A female patient aged around 70; a skin lesion imaged with a dermatoscope: 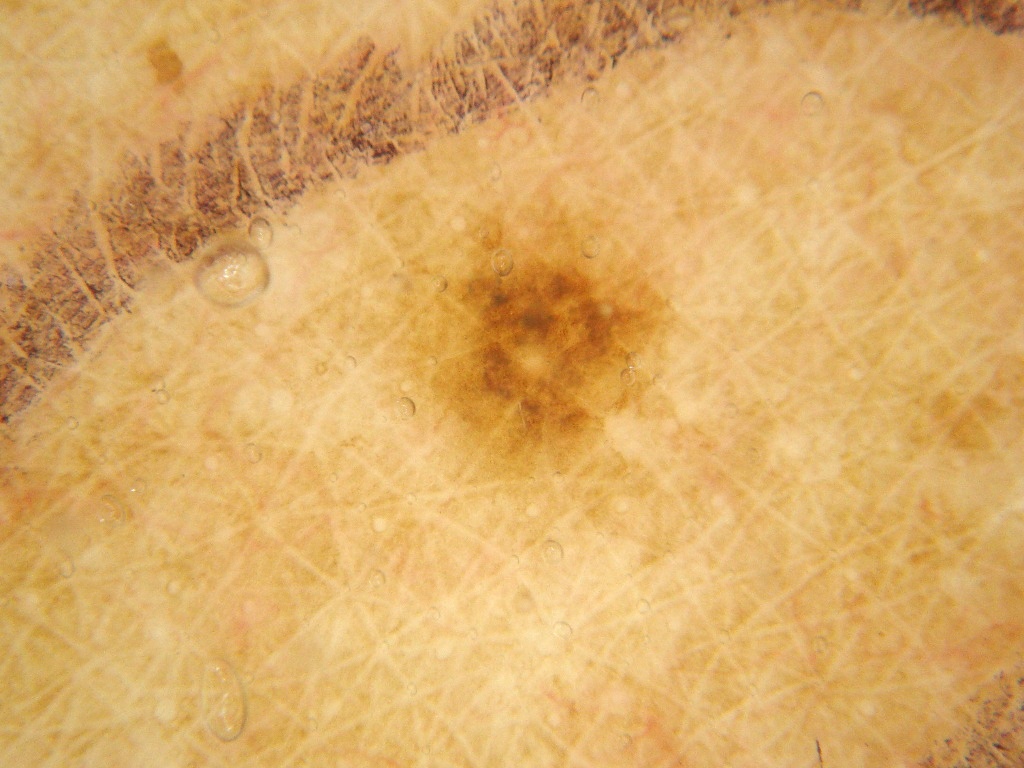Findings:
• lesion bbox — left=440, top=217, right=658, bottom=456
• lesion extent — small
• absent dermoscopic findings — negative network, pigment network, streaks, milia-like cysts, and globules
• diagnosis — a melanocytic nevus